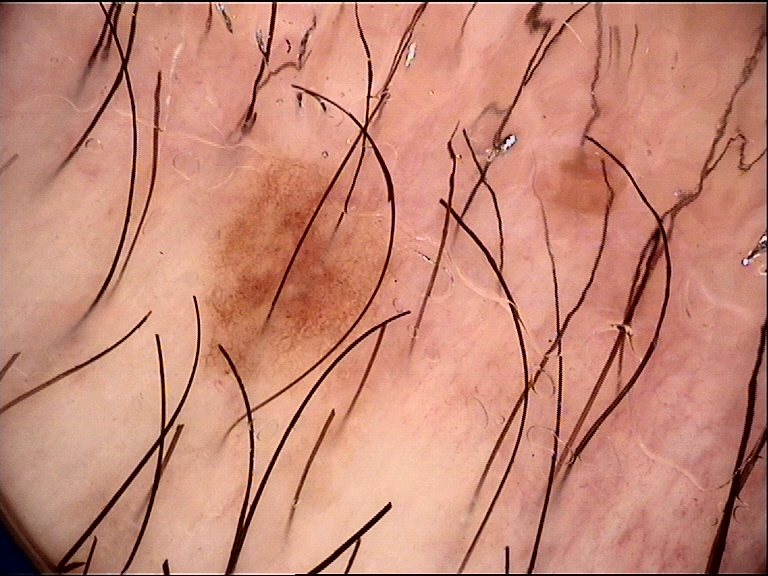<lesion>
<diagnosis>
<name>dysplastic junctional nevus</name>
<code>jd</code>
<malignancy>benign</malignancy>
<super_class>melanocytic</super_class>
<confirmation>expert consensus</confirmation>
</diagnosis>
</lesion>